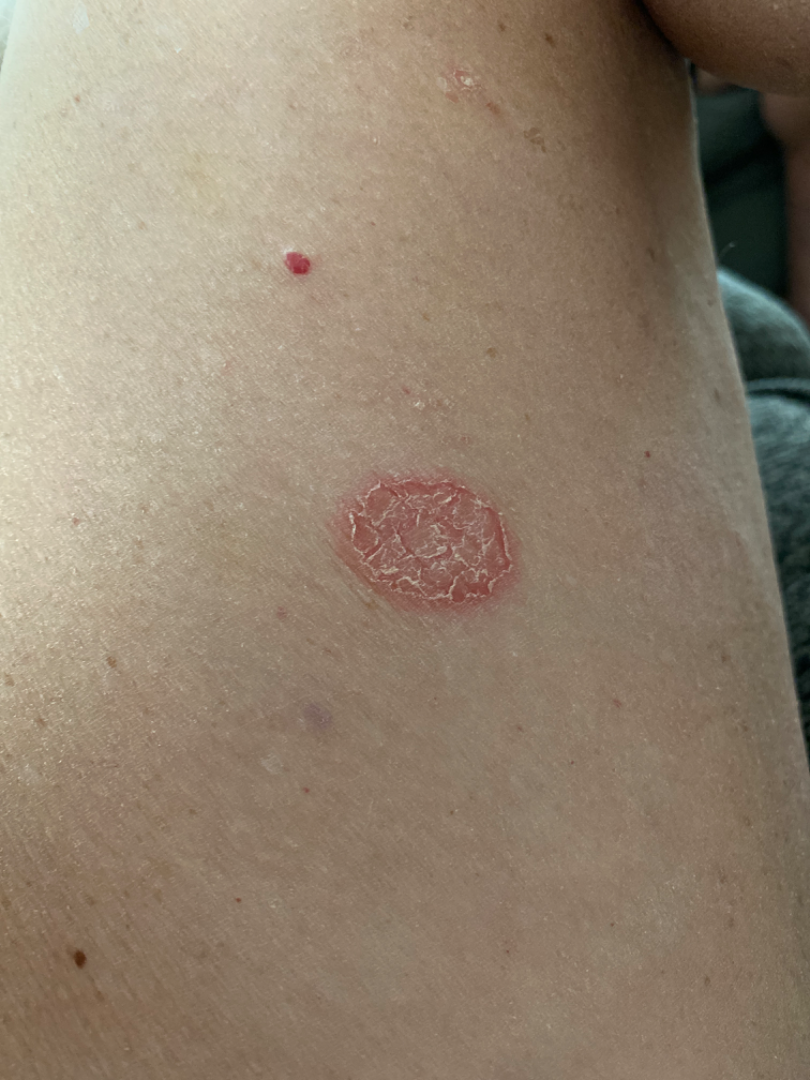No associated lesion symptoms were reported.
Located on the leg.
The patient considered this a rash.
Close-up view.
No relevant systemic symptoms.
Texture is reported as flat and rough or flaky.
On remote review of the image, Eczema (most likely).